A dermoscopic image of a skin lesion.
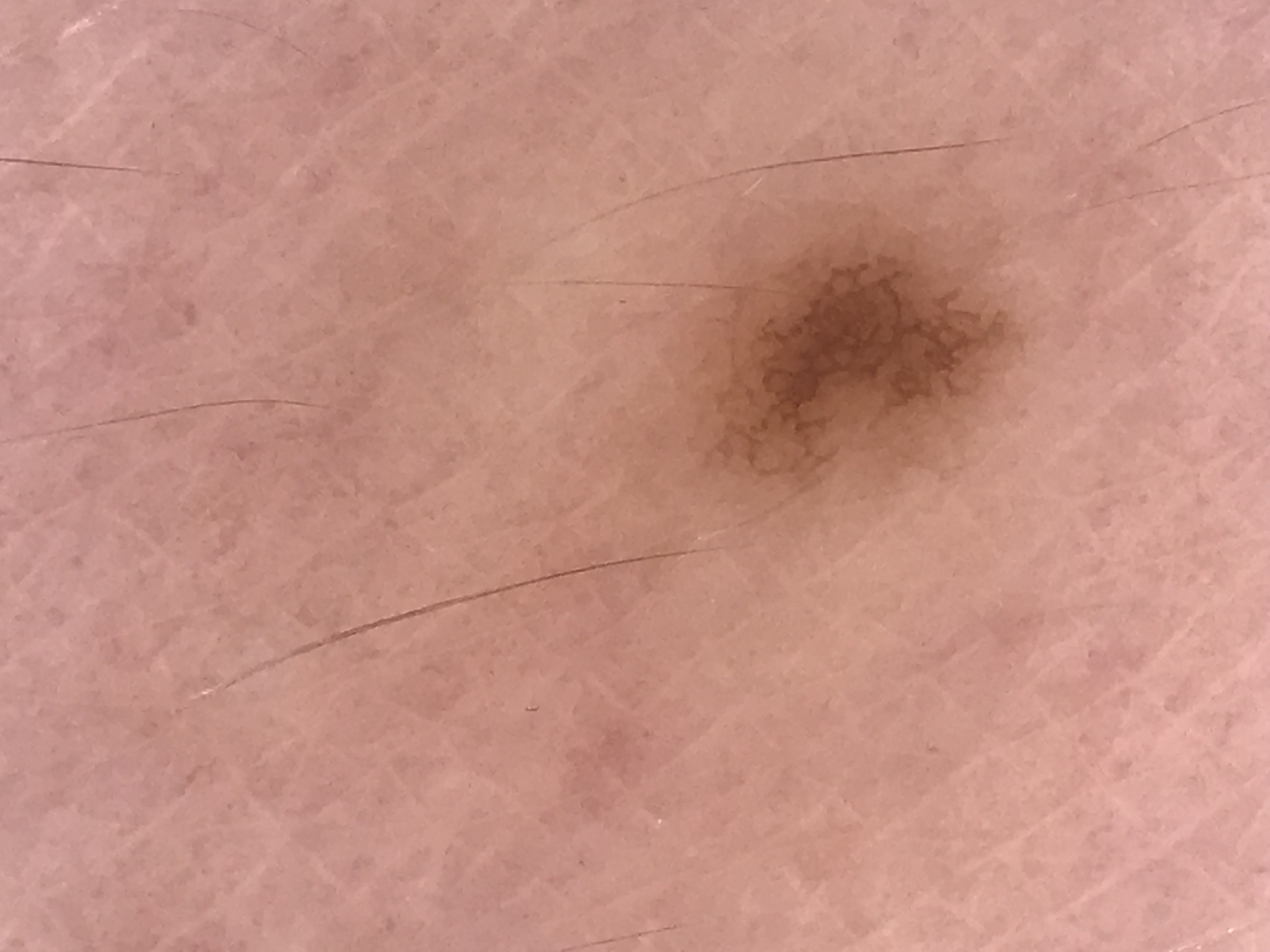Q: What kind of lesion is this?
A: banal
Q: What is the diagnosis?
A: junctional nevus (expert consensus)